The front of the torso and head or neck are involved. An image taken at an angle. Female subject, age 18–29 — 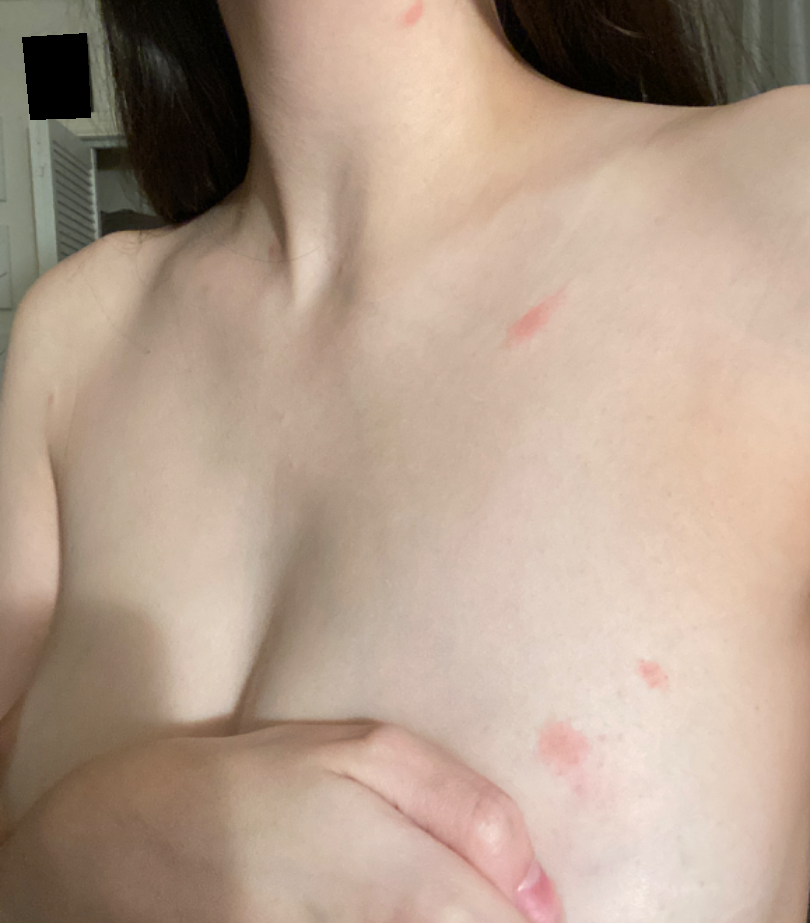The skin findings could not be characterized from the image.